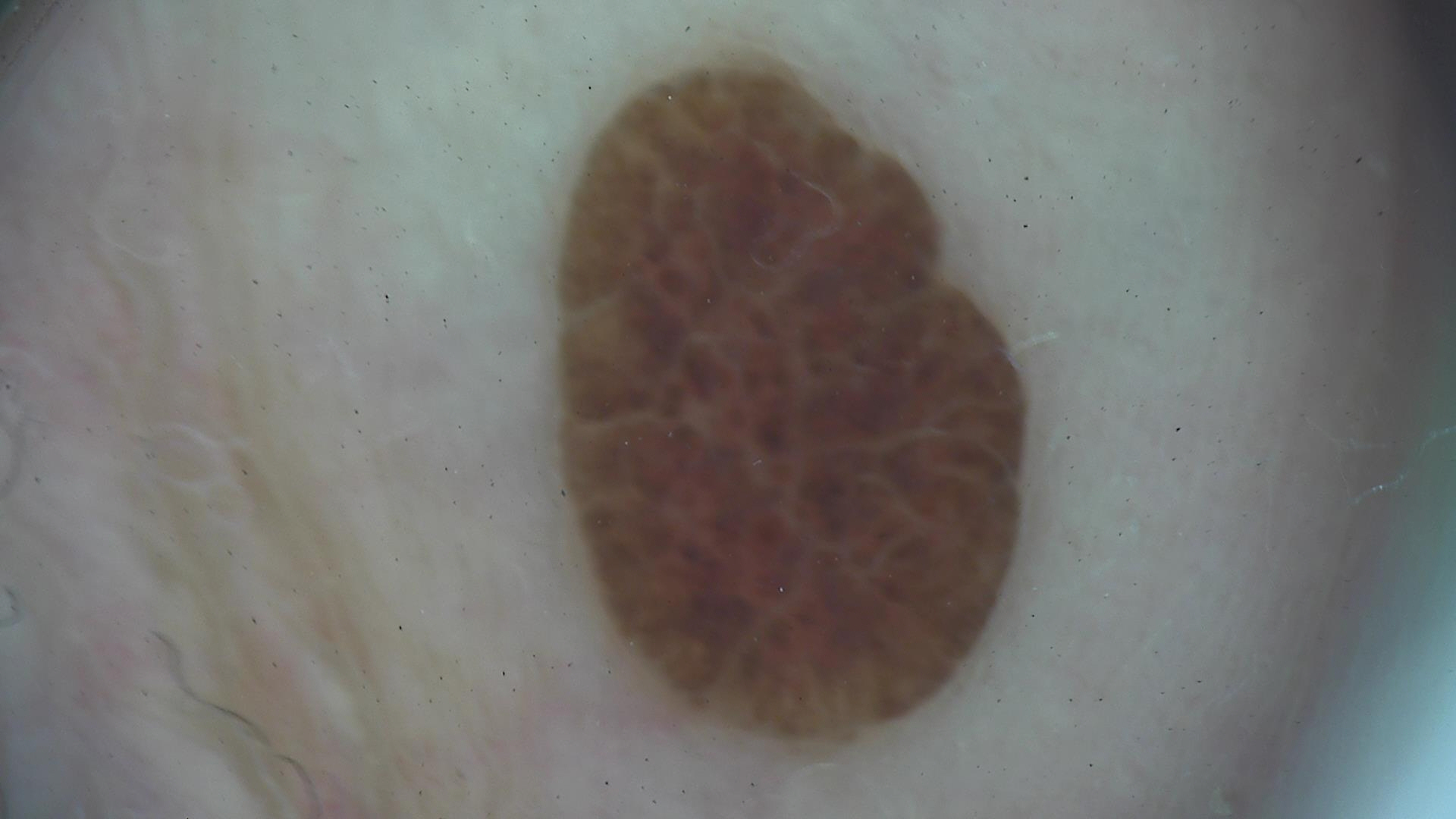Diagnosed as a banal lesion — a compound nevus.